Close-up view · the patient is a female aged 40–49 · the affected area is the head or neck:
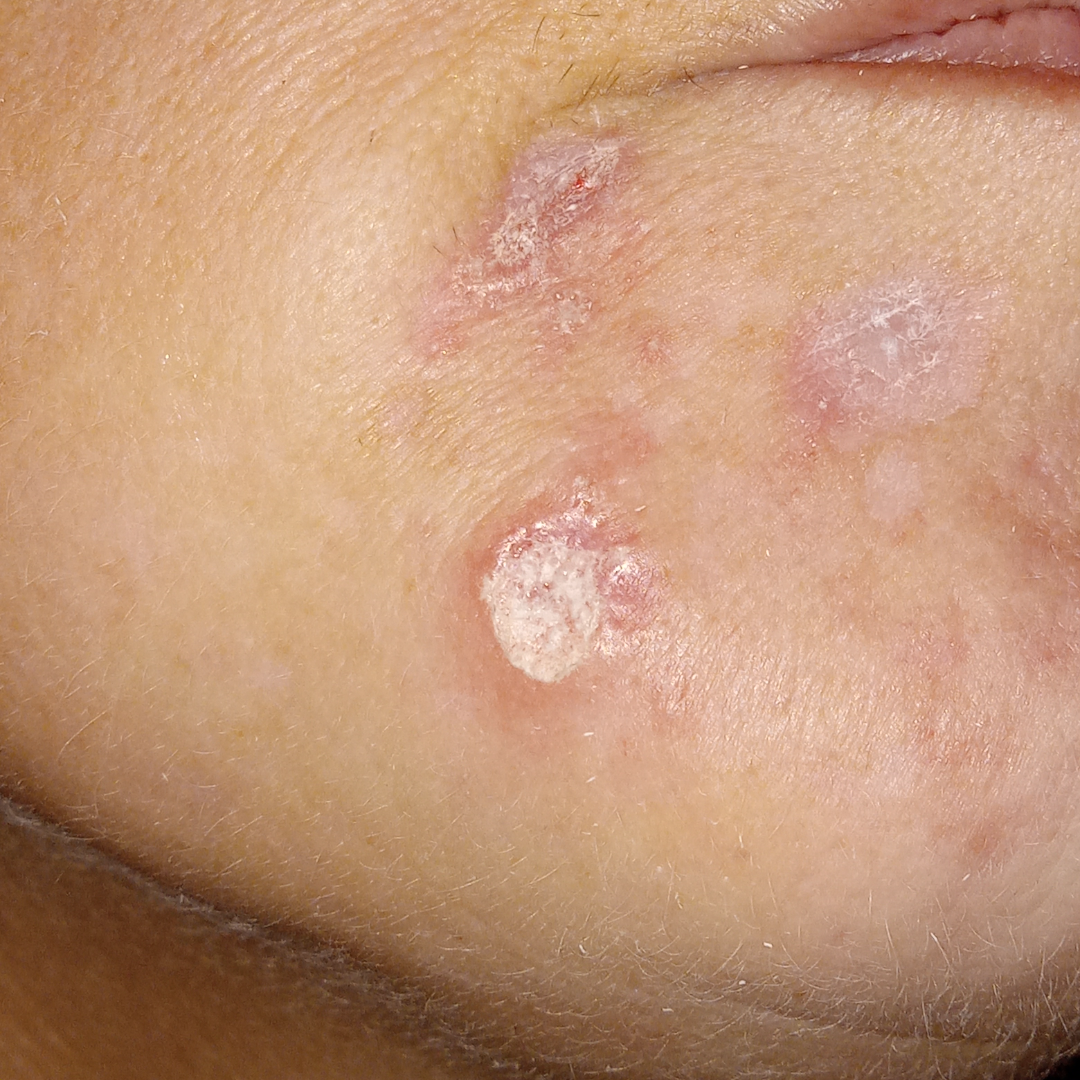• assessment · ungradable on photographic review